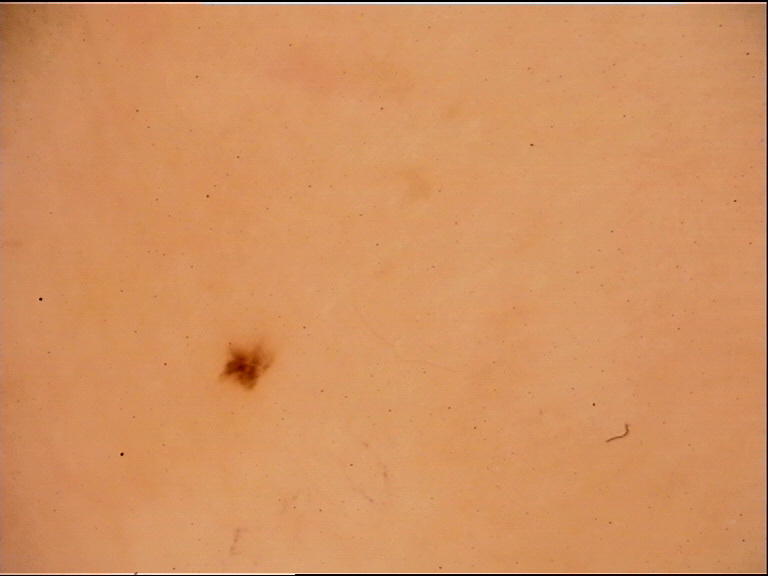<lesion>
  <image>dermoscopy</image>
  <diagnosis>
    <name>acral dysplastic junctional nevus</name>
    <code>ajd</code>
    <malignancy>benign</malignancy>
    <super_class>melanocytic</super_class>
    <confirmation>expert consensus</confirmation>
  </diagnosis>
</lesion>